Located on the head or neck, arm and front of the torso; the patient considered this a rash; no relevant systemic symptoms; the contributor reports the lesion is raised or bumpy; reported lesion symptoms include enlargement, bothersome appearance and itching; close-up view; the contributor reports the condition has been present for less than one week — 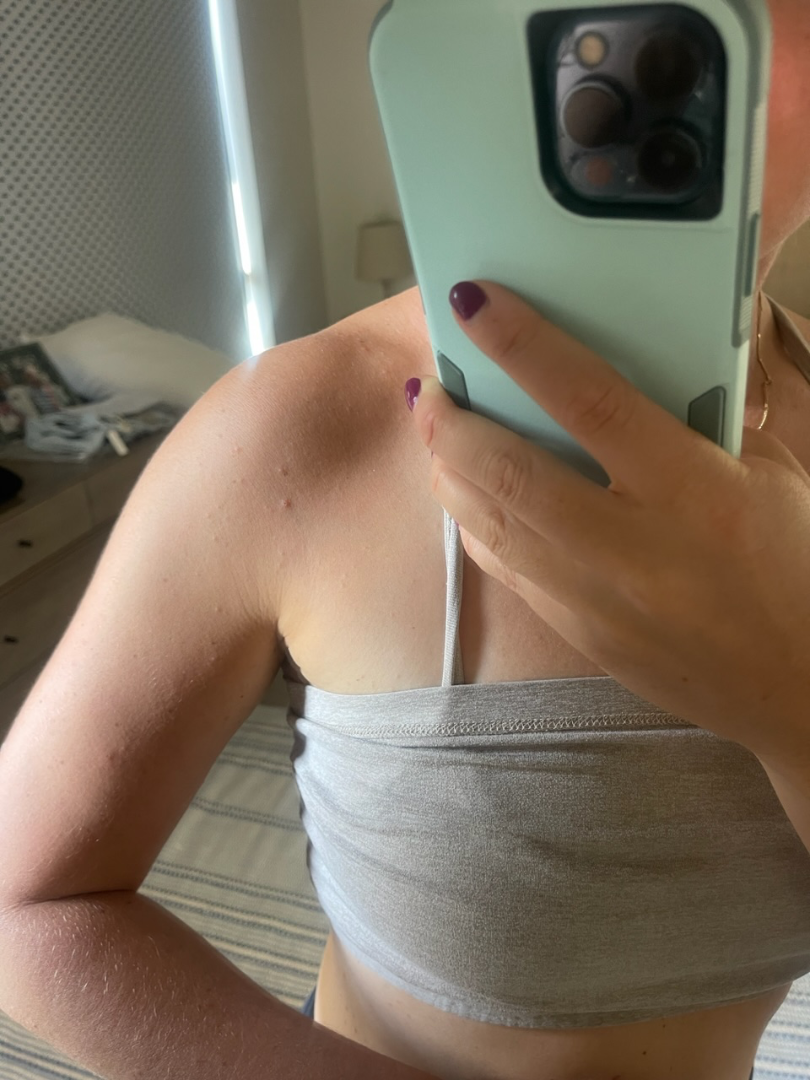The dermatologist could not determine a likely condition from the photograph alone.